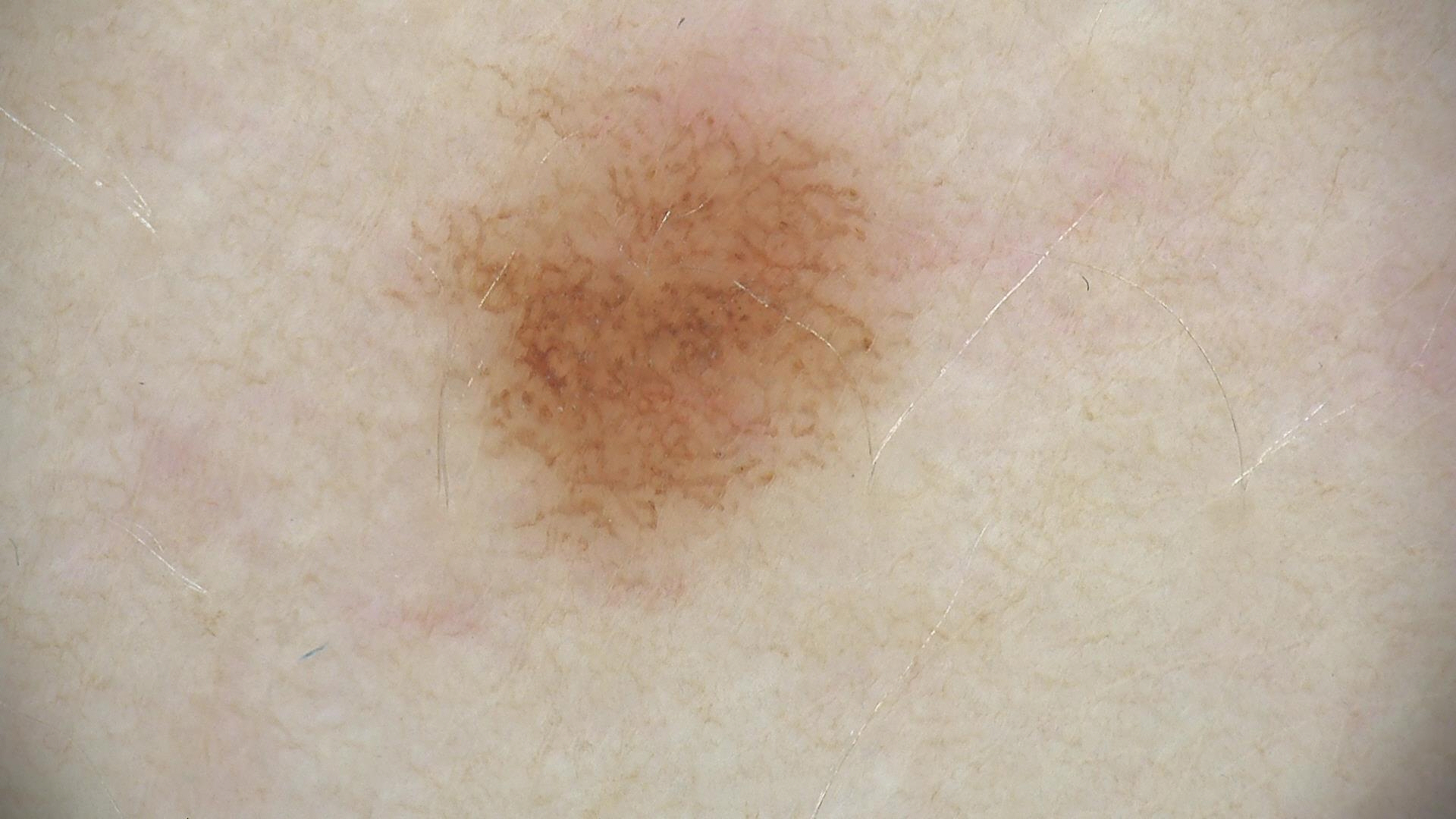{
  "image": "dermatoscopy",
  "diagnosis": {
    "name": "dysplastic junctional nevus",
    "code": "jd",
    "malignancy": "benign",
    "super_class": "melanocytic",
    "confirmation": "expert consensus"
  }
}